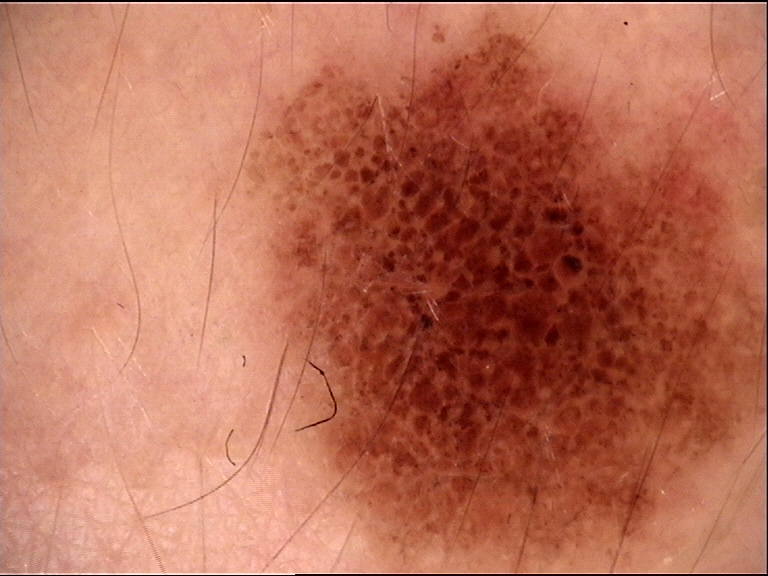class = dysplastic compound nevus (expert consensus).